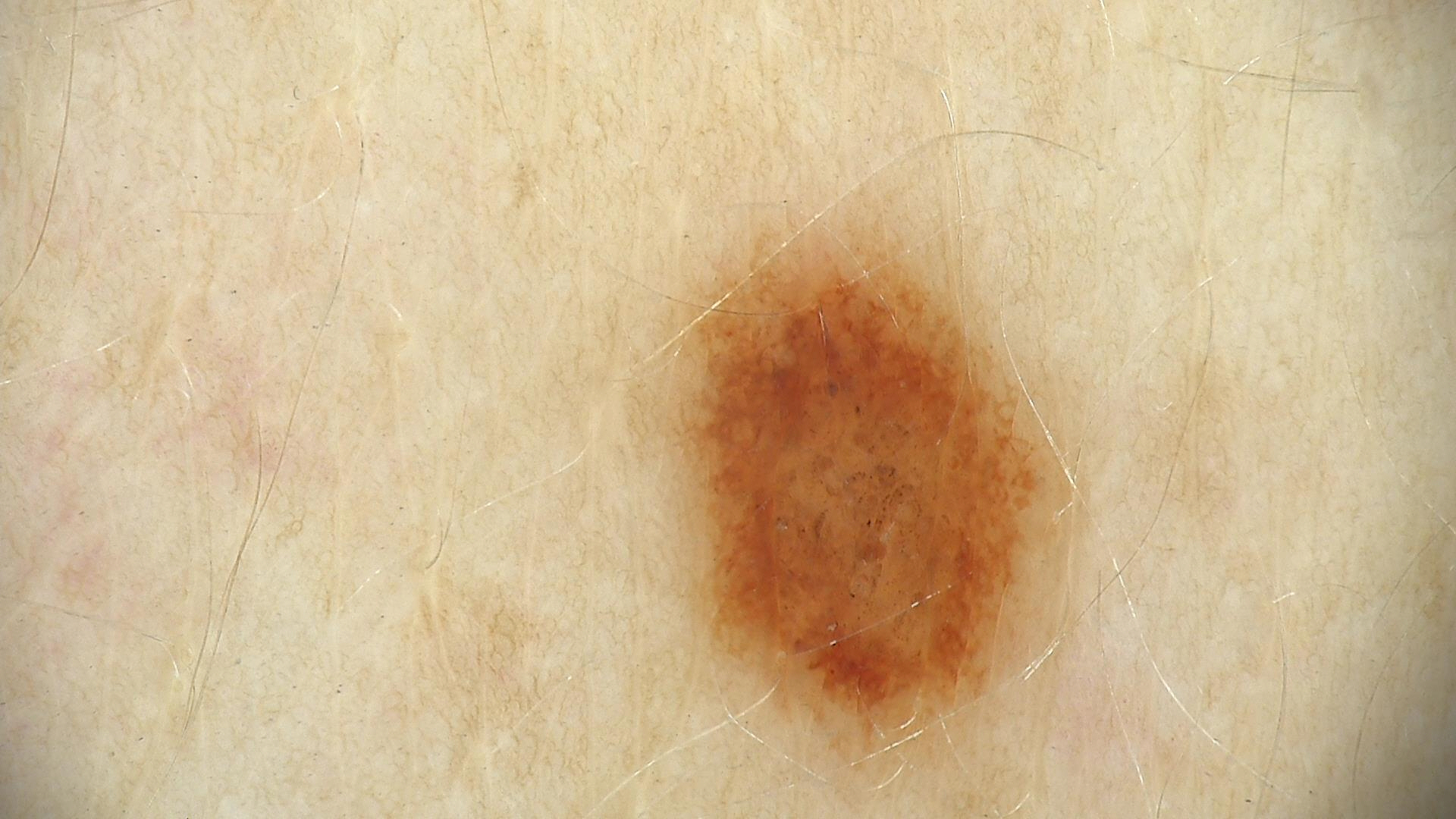label — dysplastic compound nevus (expert consensus)